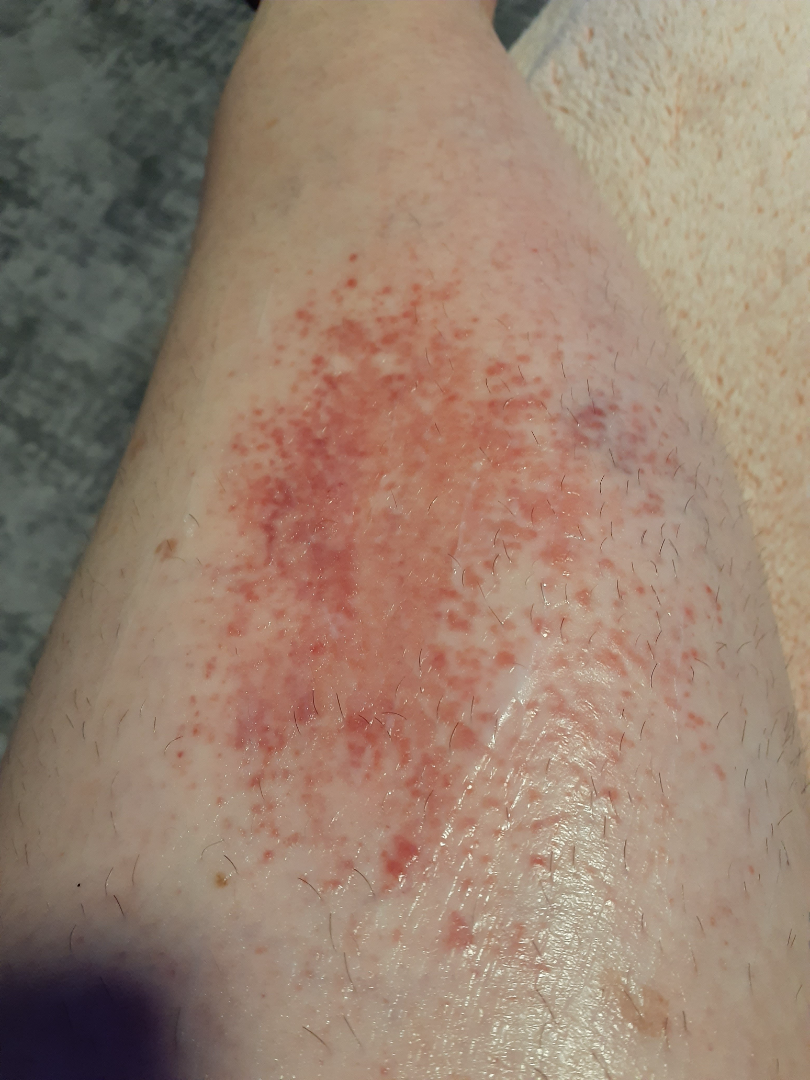Background:
This is a close-up image. Skin tone: Fitzpatrick skin type III; lay reviewers estimated Monk Skin Tone 2 or 3. The lesion involves the leg. Female subject, age 50–59. The condition has been present for three to twelve months. Self-categorized by the patient as a rash. Texture is reported as raised or bumpy. The lesion is associated with itching, enlargement and bothersome appearance.
Findings:
Allergic Contact Dermatitis (weight 0.25); Eczema (weight 0.20); Stasis Dermatitis (weight 0.14); Burn of skin (weight 0.14); Acute dermatitis, NOS (weight 0.11); Irritant Contact Dermatitis (weight 0.11); Pretibial myxedema (weight 0.06).